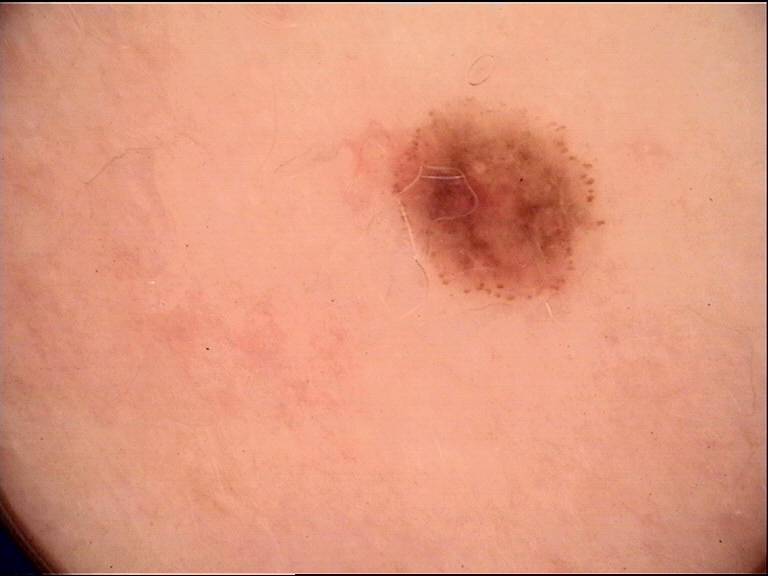class=dysplastic compound nevus (expert consensus).